The leg is involved; the photograph is a close-up of the affected area: 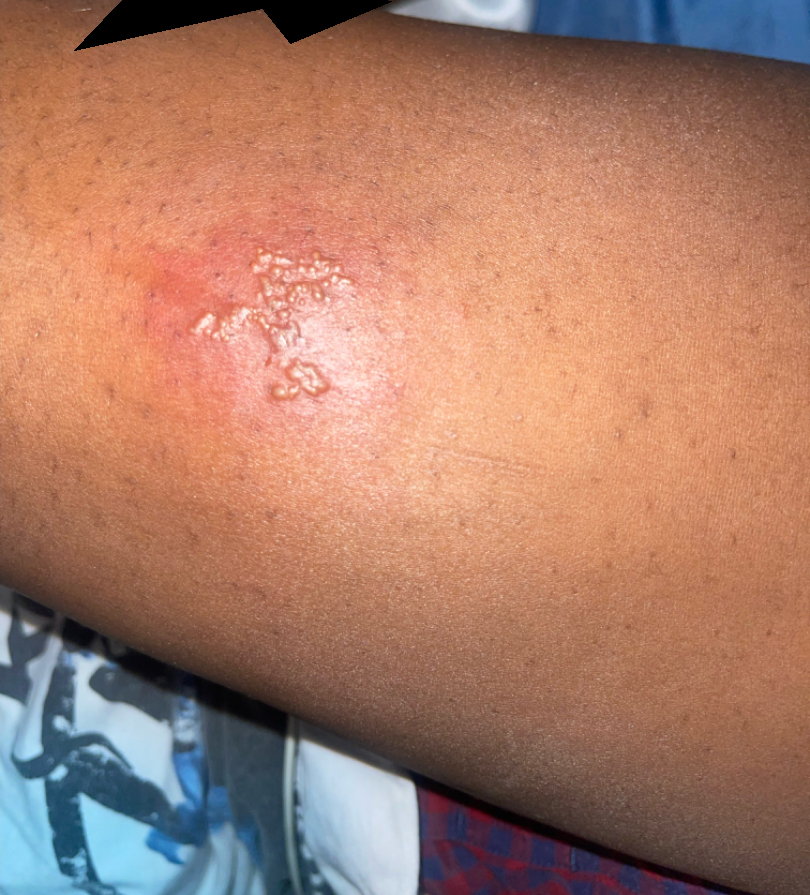symptoms = itching, pain and bothersome appearance | texture = raised or bumpy and fluid-filled | associated systemic symptoms = joint pain | dermatologist impression = Herpes Simplex (most likely); Cellulitis (considered); Lymphangioma (considered).